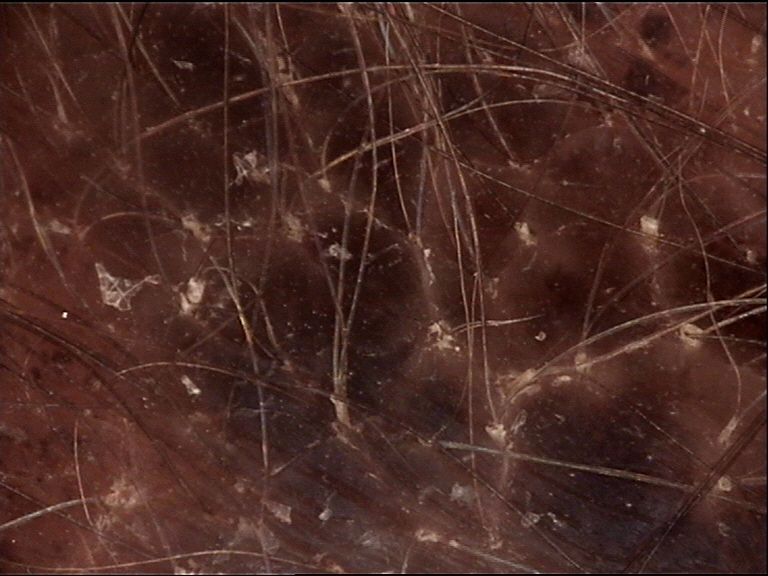Impression:
Classified as a congenital compound nevus.